A dermoscopic image of a skin lesion.
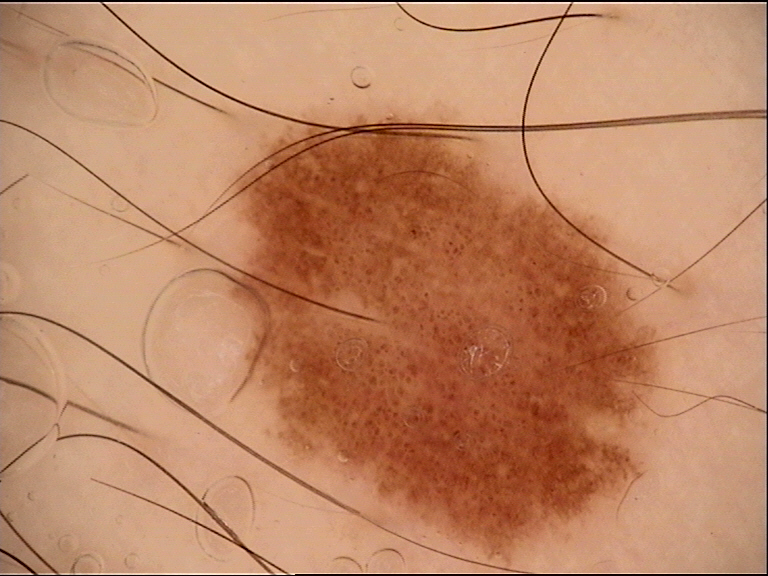Conclusion: The diagnostic label was a dysplastic junctional nevus.